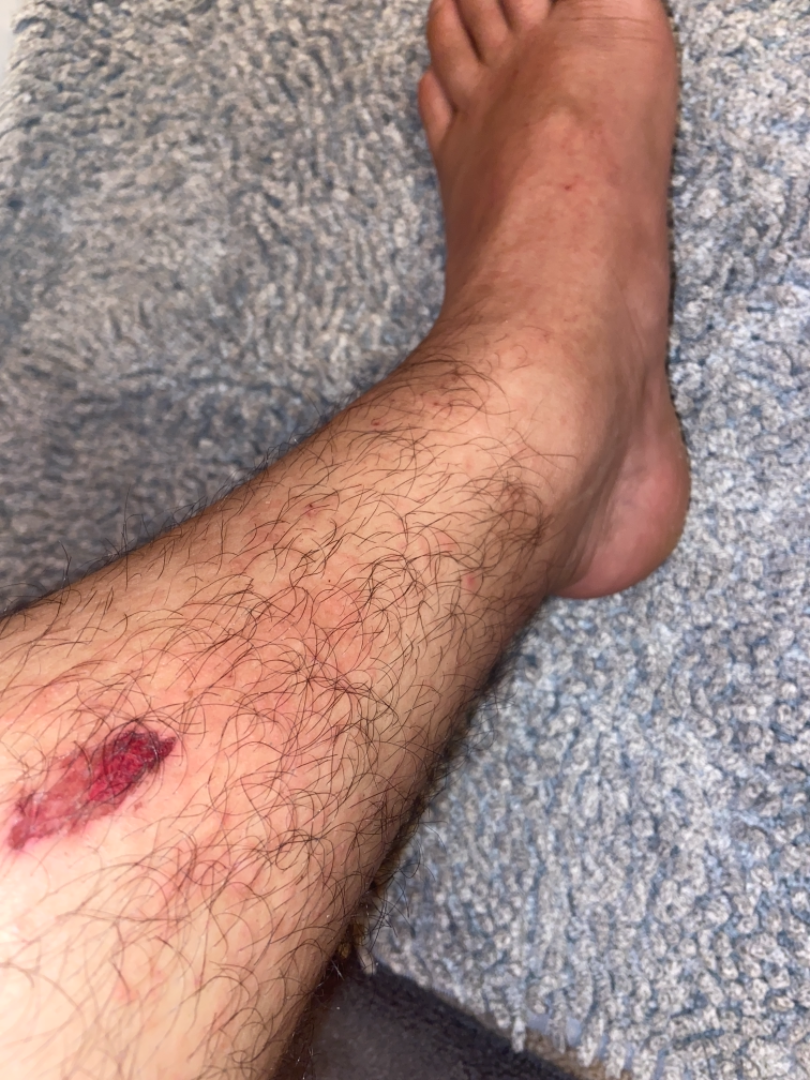| field | value |
|---|---|
| assessment | indeterminate |
| contributor | male, age 18–29 |
| anatomic site | leg |
| image framing | close-up |